A dermoscopic close-up of a skin lesion: 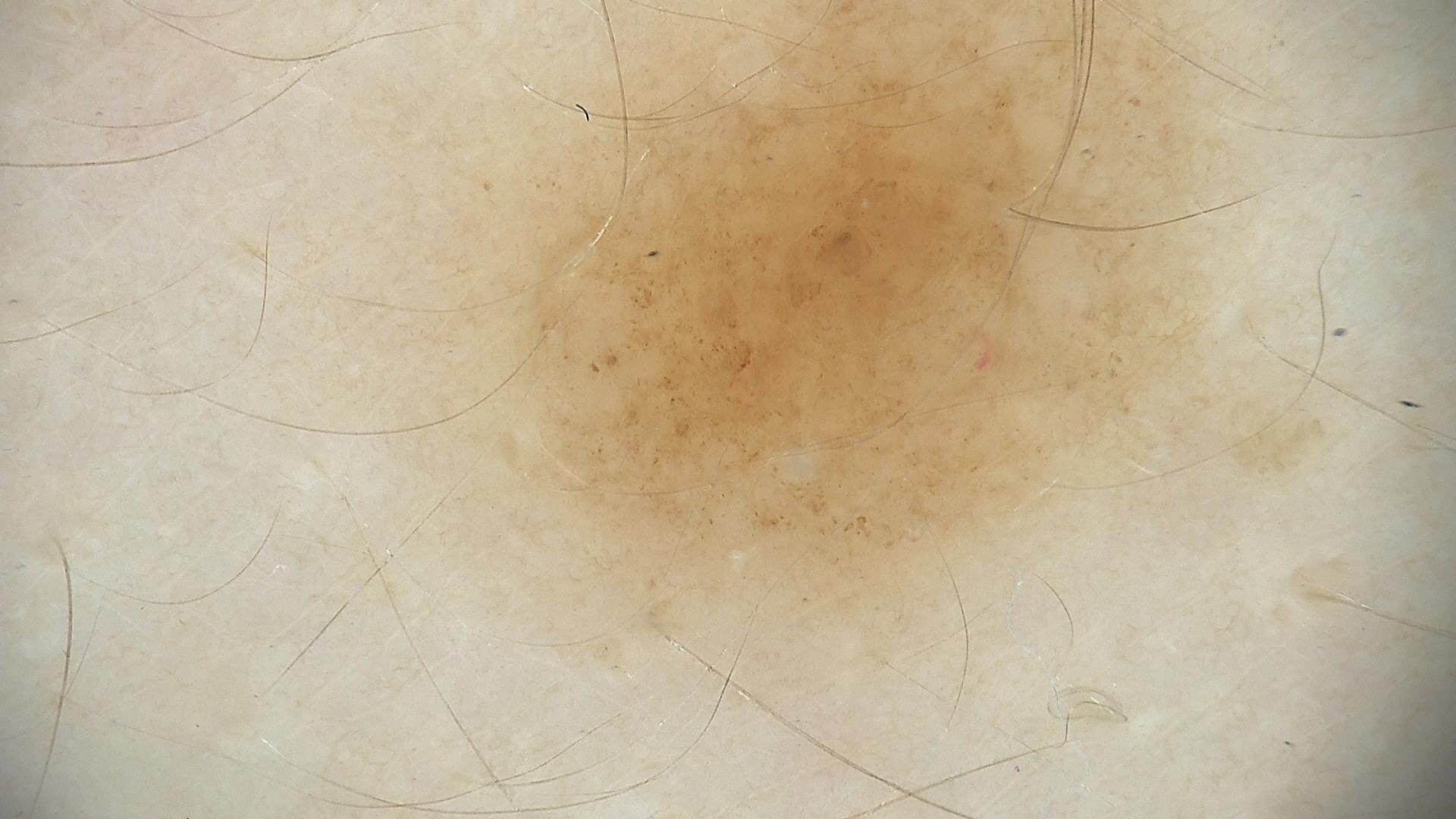Classified as a compound nevus.